Close-up view. The lesion is described as raised or bumpy. Reported duration is less than one week. The lesion is associated with itching, enlargement and burning. The patient considered this a rash. The leg, back of the torso, head or neck, arm and front of the torso are involved:
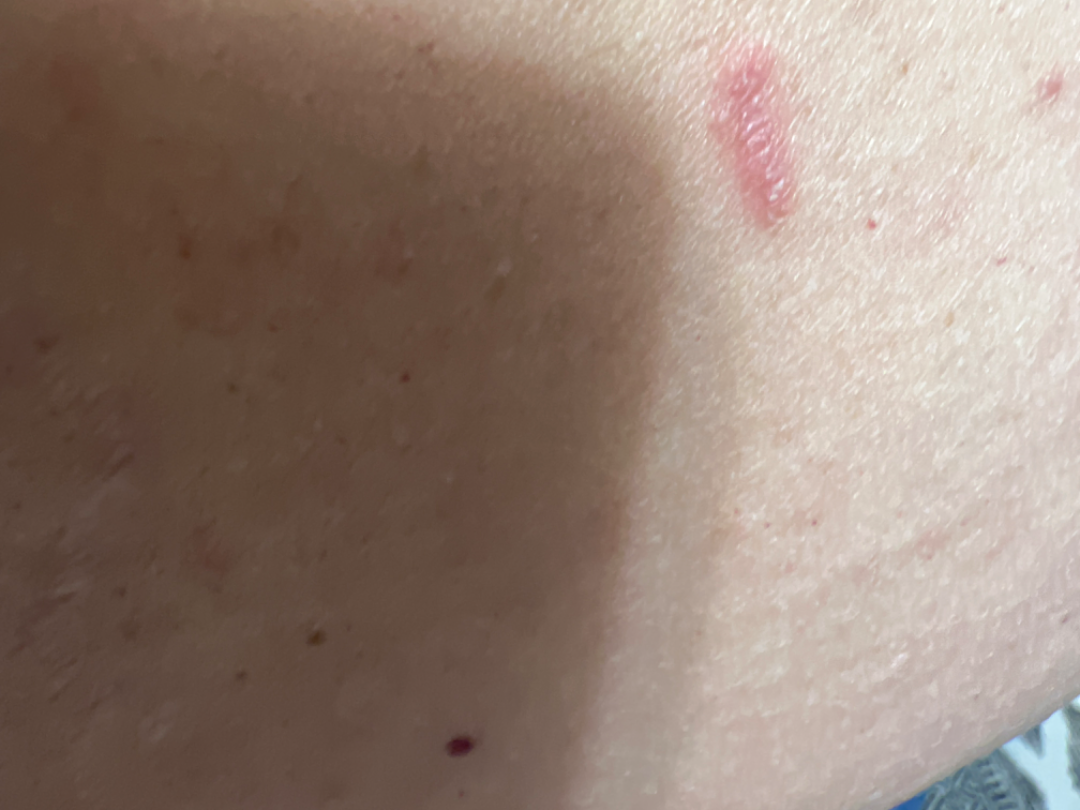Q: What is the differential diagnosis?
A: the differential includes Pyoderma, Insect Bite and Allergic Contact Dermatitis, with no clear leading consideration